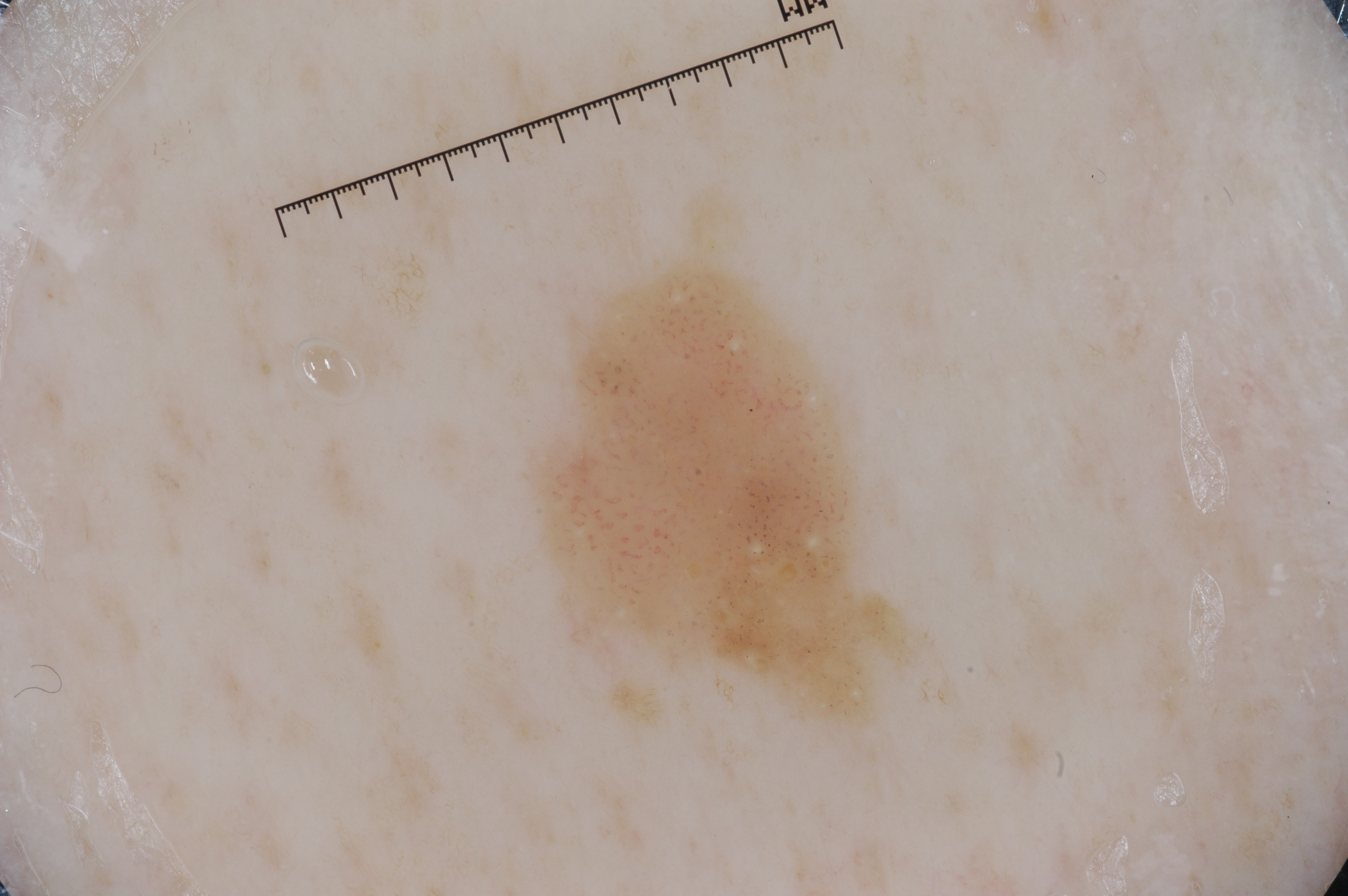Case summary:
– image type · dermoscopic image
– features · pigment network and milia-like cysts; absent: negative network and streaks
– lesion bbox · box(537, 259, 906, 707)
– extent · ~9% of the field
– impression · a seborrheic keratosis, a keratinocytic lesion